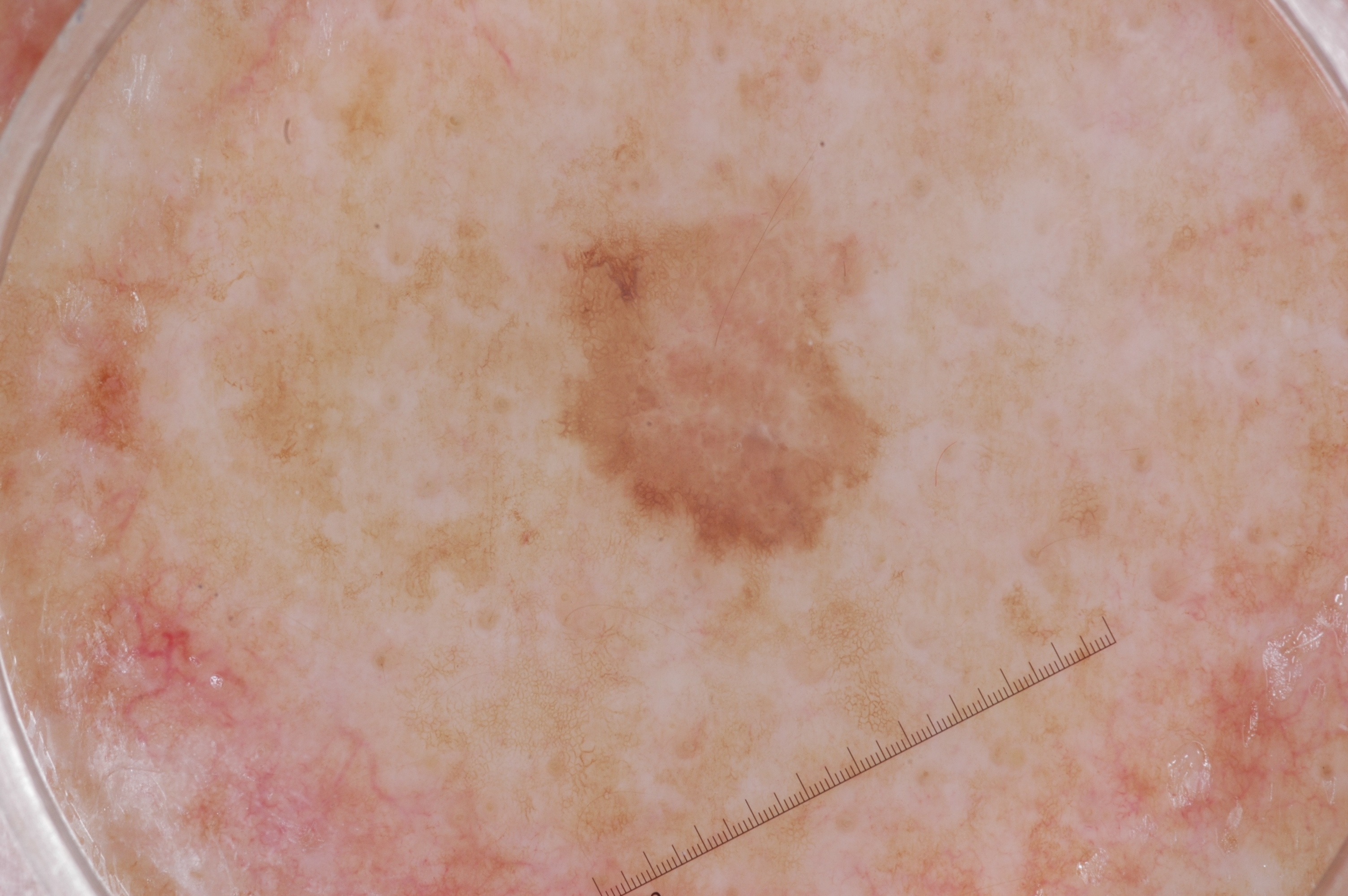Case summary:
A dermoscopy image of a single skin lesion. The lesion occupies the region bbox=[537, 175, 889, 646].
Conclusion:
The diagnostic assessment was a melanocytic nevus.